A dermoscopic view of a skin lesion — 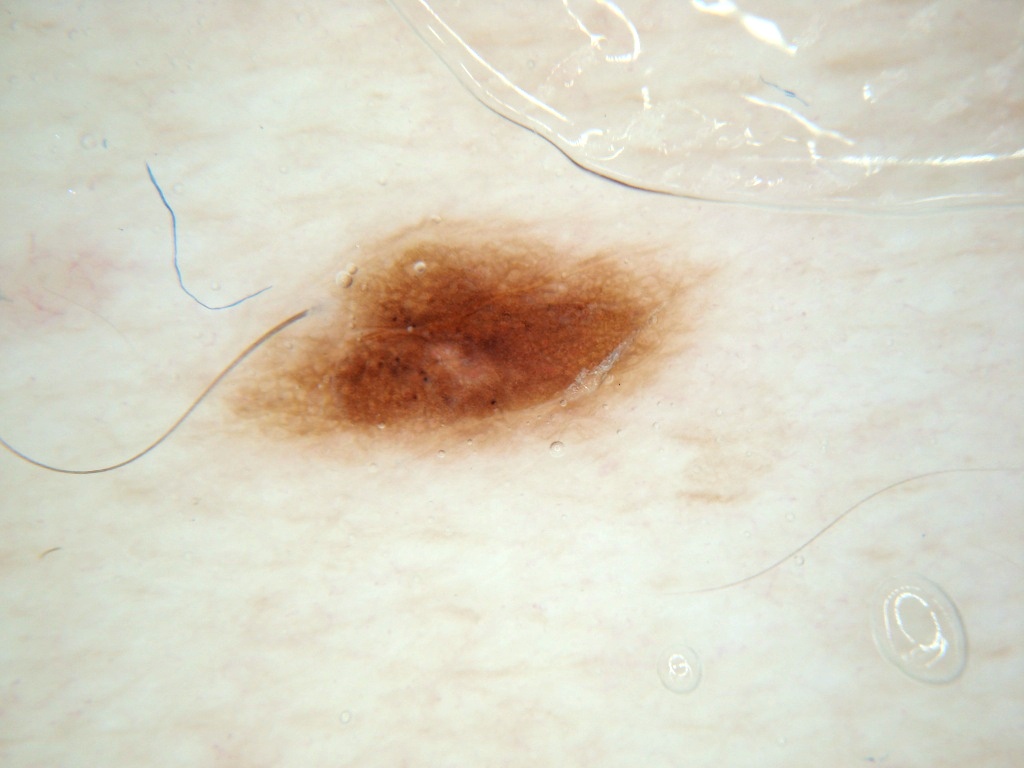Image and clinical context: The visible lesion spans 203/209/724/482. Assessment: Diagnosed as a melanocytic nevus, a benign lesion.